A male subject aged 68-72. FST II — 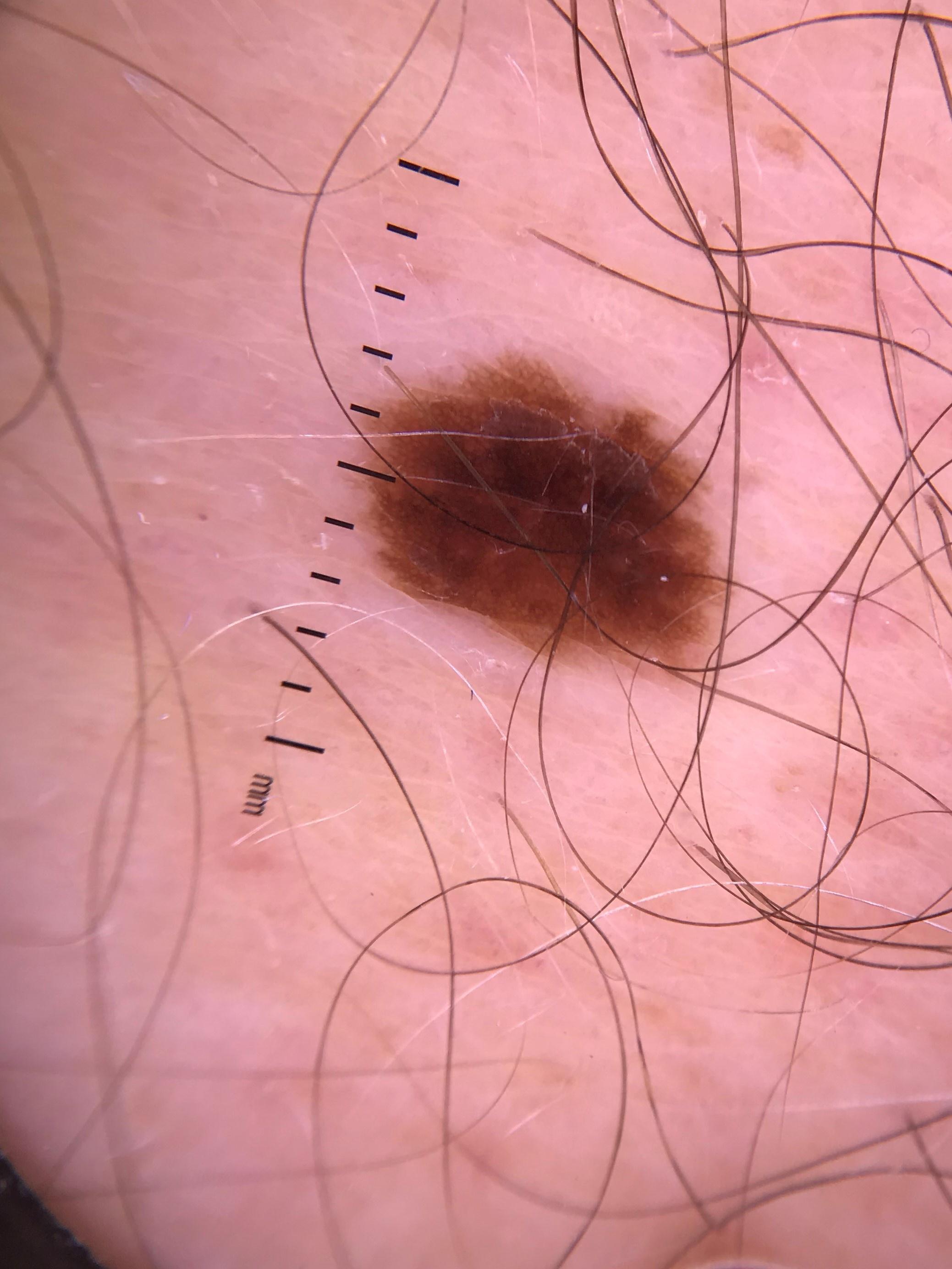Clinically diagnosed as a nevus.